The affected area is the arm, an image taken at an angle.
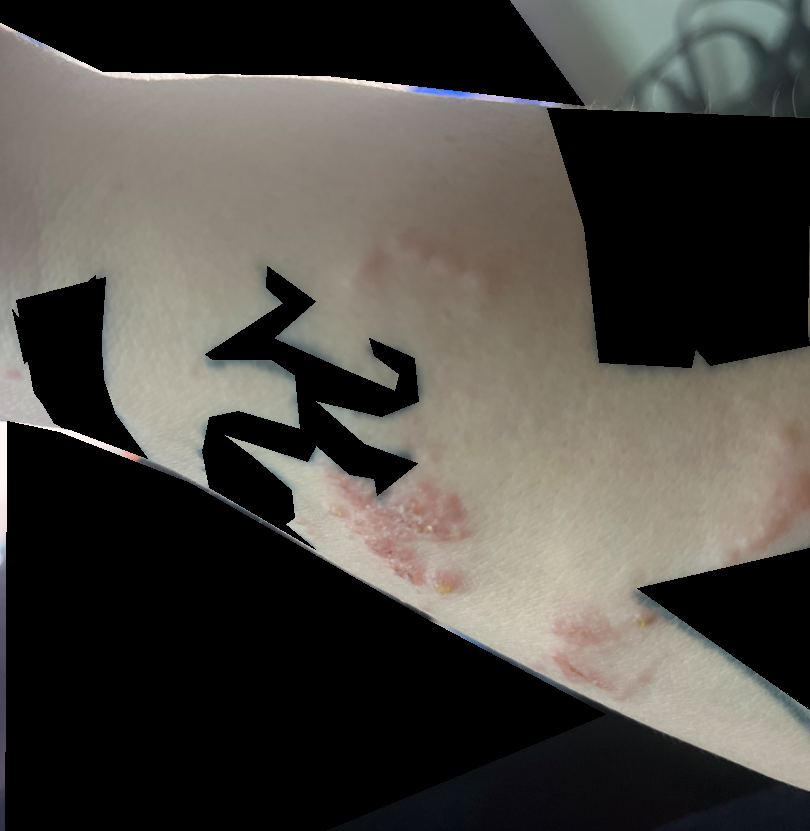  assessment: not assessable